Female contributor, age 30–39. This image was taken at an angle. The back of the hand and front of the torso are involved: 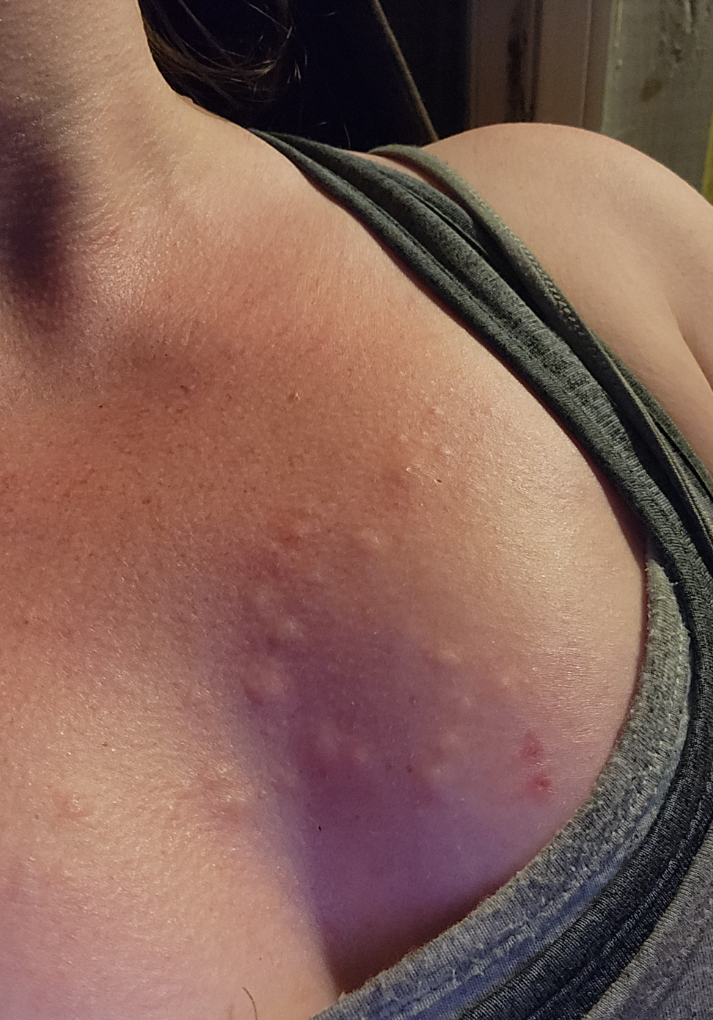  assessment: could not be assessed
  duration: less than one week
  texture: raised or bumpy
  patient_category: a rash